Female contributor, age 40–49. A close-up photograph. The head or neck is involved:
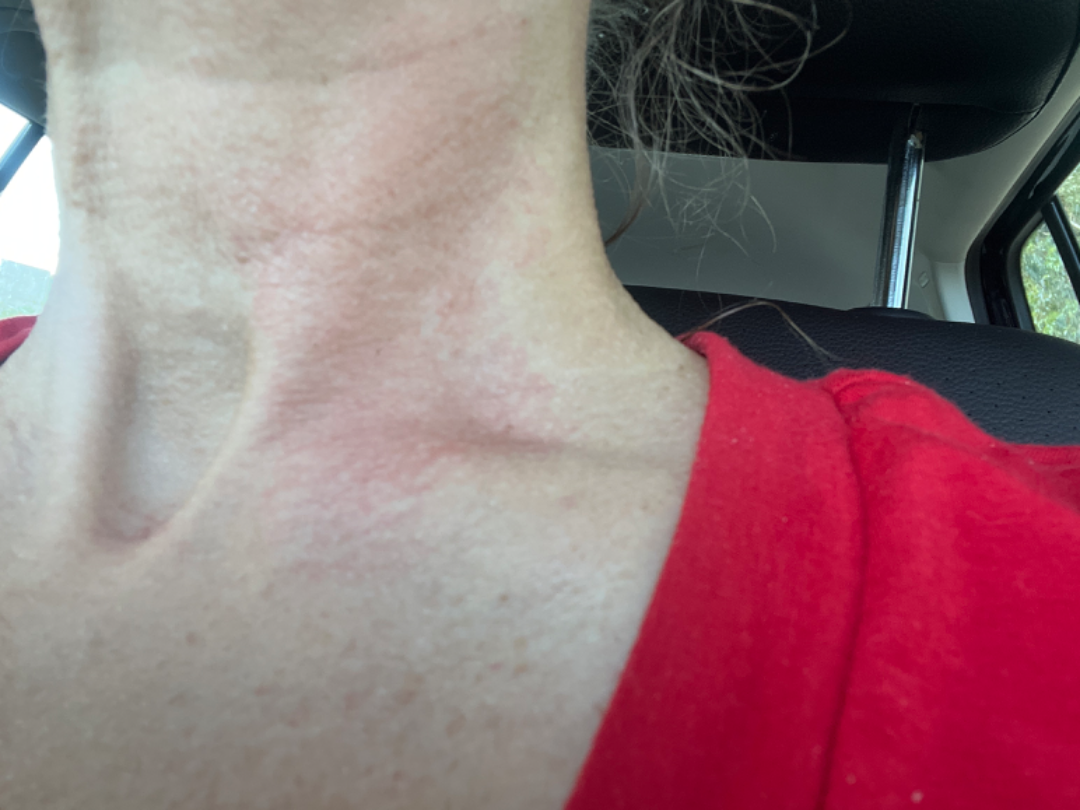Background: No relevant systemic symptoms. Present for about one day. Self-categorized by the patient as a rash. Reported lesion symptoms include burning. Findings: On dermatologist assessment of the image: Allergic Contact Dermatitis and Irritant Contact Dermatitis were considered with similar weight.